Dermoscopy of a skin lesion:
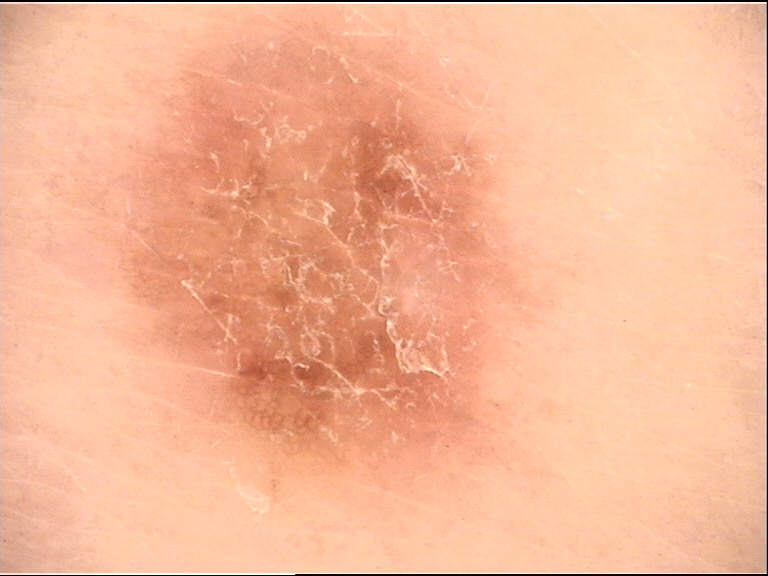* category · banal
* label · junctional nevus (expert consensus)